A dermoscopic image of a skin lesion:
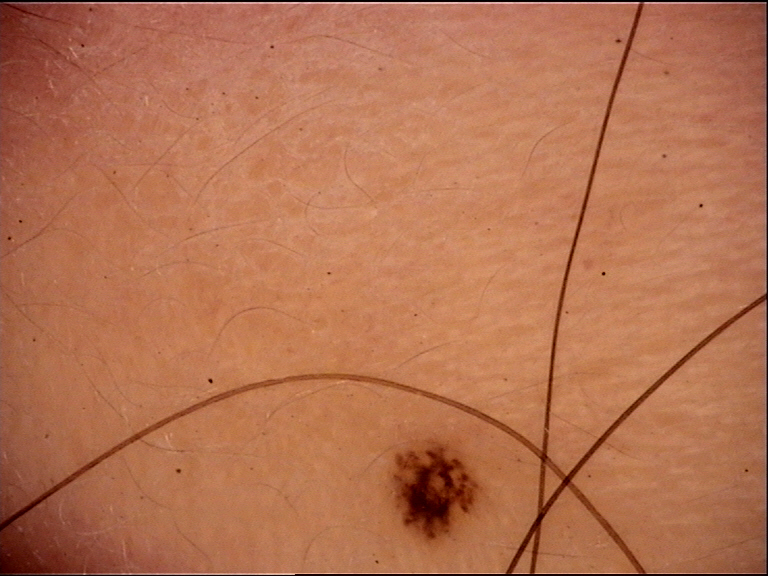diagnostic label=junctional nevus (expert consensus)